The patient describes having numerous moles. A dermoscopy image of a skin lesion. A female patient age 54. Imaged for a research study, with no referral diagnosis recorded. By self-report, a personal history of cancer, a personal history of skin cancer, and a family history of skin cancer. The patient says their skin reddens with sun exposure.
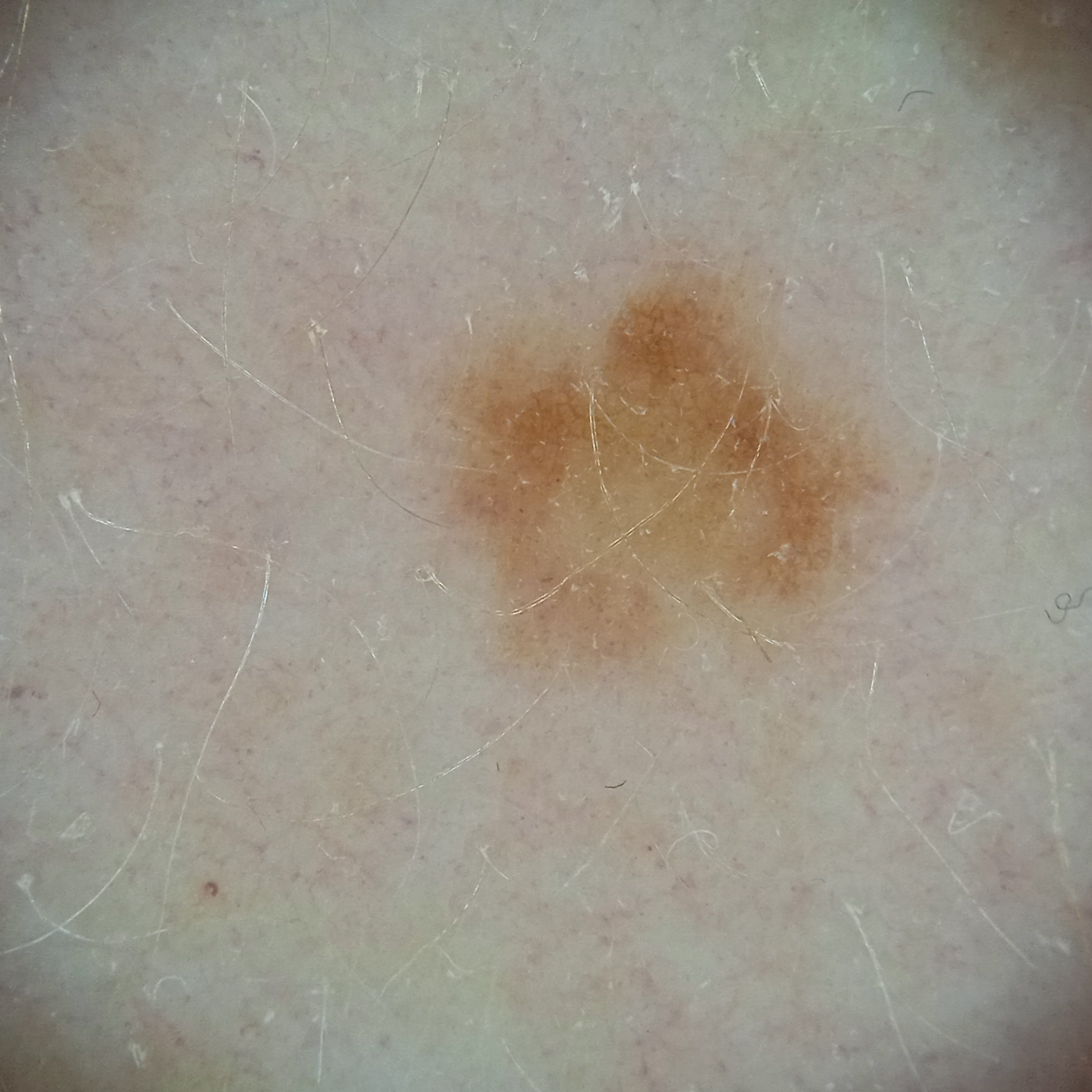Findings:
• site: an arm
• size: 4.7 mm
• assessment: atypical (dysplastic) nevus — dermatologist consensus